The patient says their skin reddens painfully with sun exposure. A macroscopic clinical photograph of a skin lesion. Imaged for a research study, with no referral diagnosis recorded.
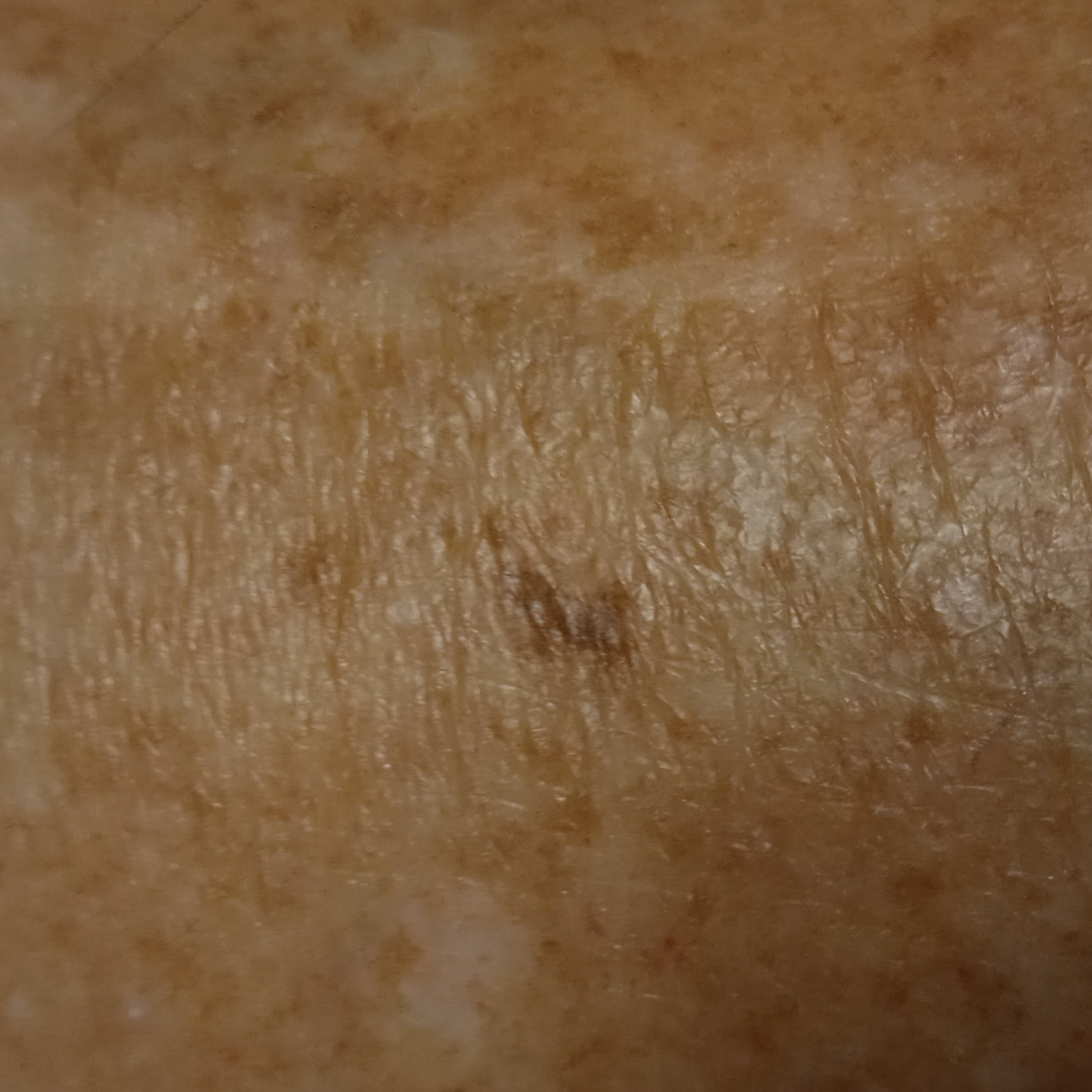Case summary: The lesion is located on a leg. Assessment: The diagnostic impression was a melanocytic nevus.